A dermoscopy image of a single skin lesion.
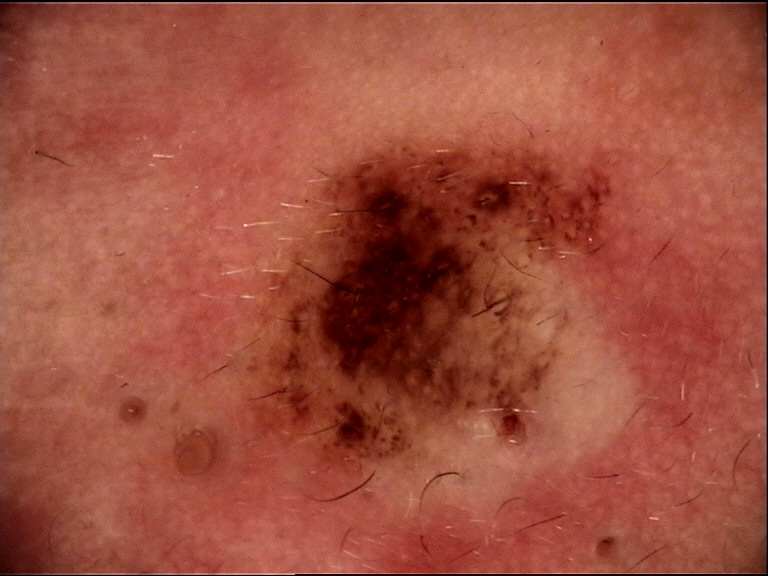Case: The morphology is that of a banal, compound lesion. Conclusion: The diagnosis was a Miescher nevus.